On a questionnaire the patient reported a family history of skin cancer and a personal history of cancer. The patient says their skin tans without first burning. A female patient aged 92: 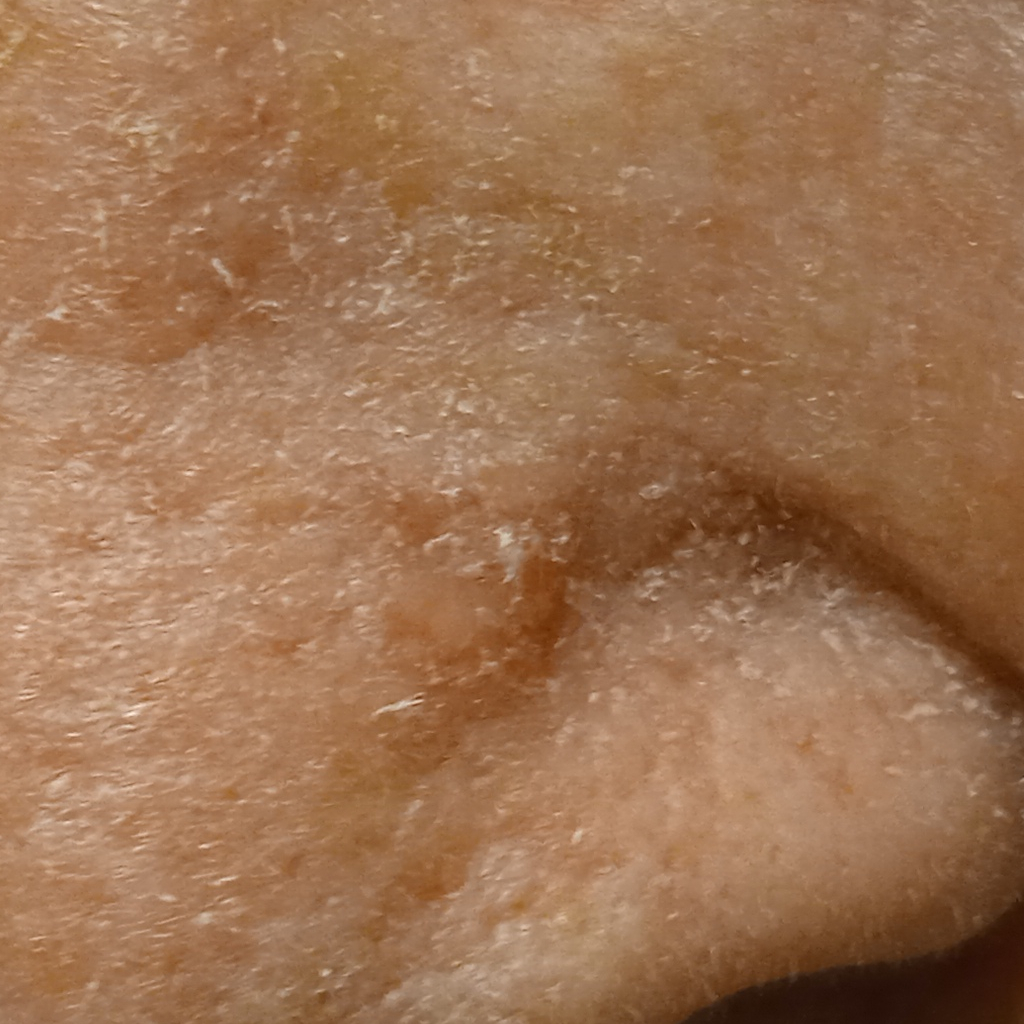The lesion is located on the face. The lesion is about 7 mm across. The dermatologists' assessment was a basal cell carcinoma.